Dermoscopy of a skin lesion.
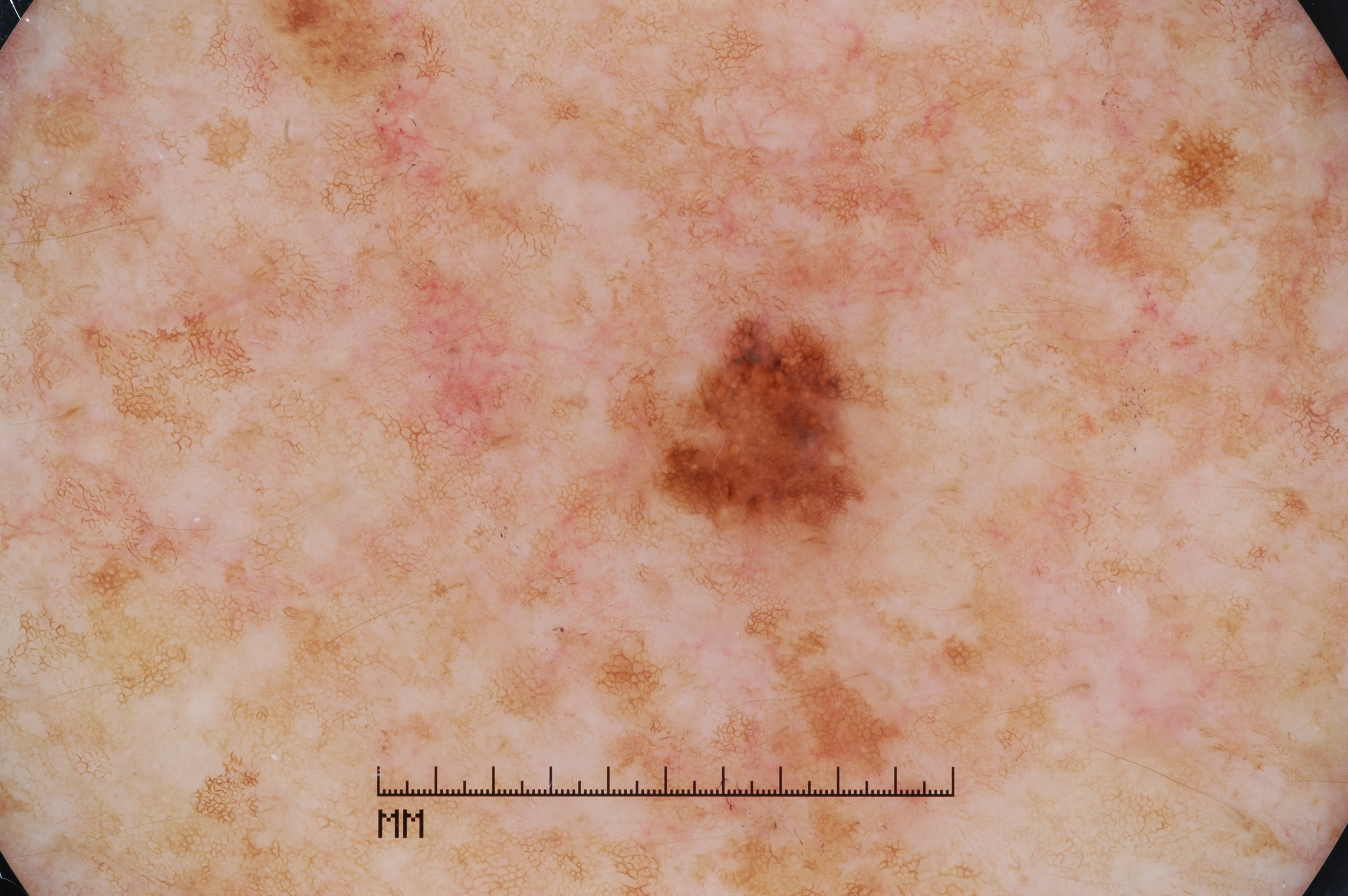As (left, top, right, bottom), the lesion spans <box>633, 322, 863, 546</box>. Consistent with a melanocytic nevus.